Acquired for a research image collection, with no referral diagnosis · on a questionnaire the patient reported a personal history of skin cancer and a personal history of cancer · a male patient age 77 · the patient says their skin reddens with sun exposure.
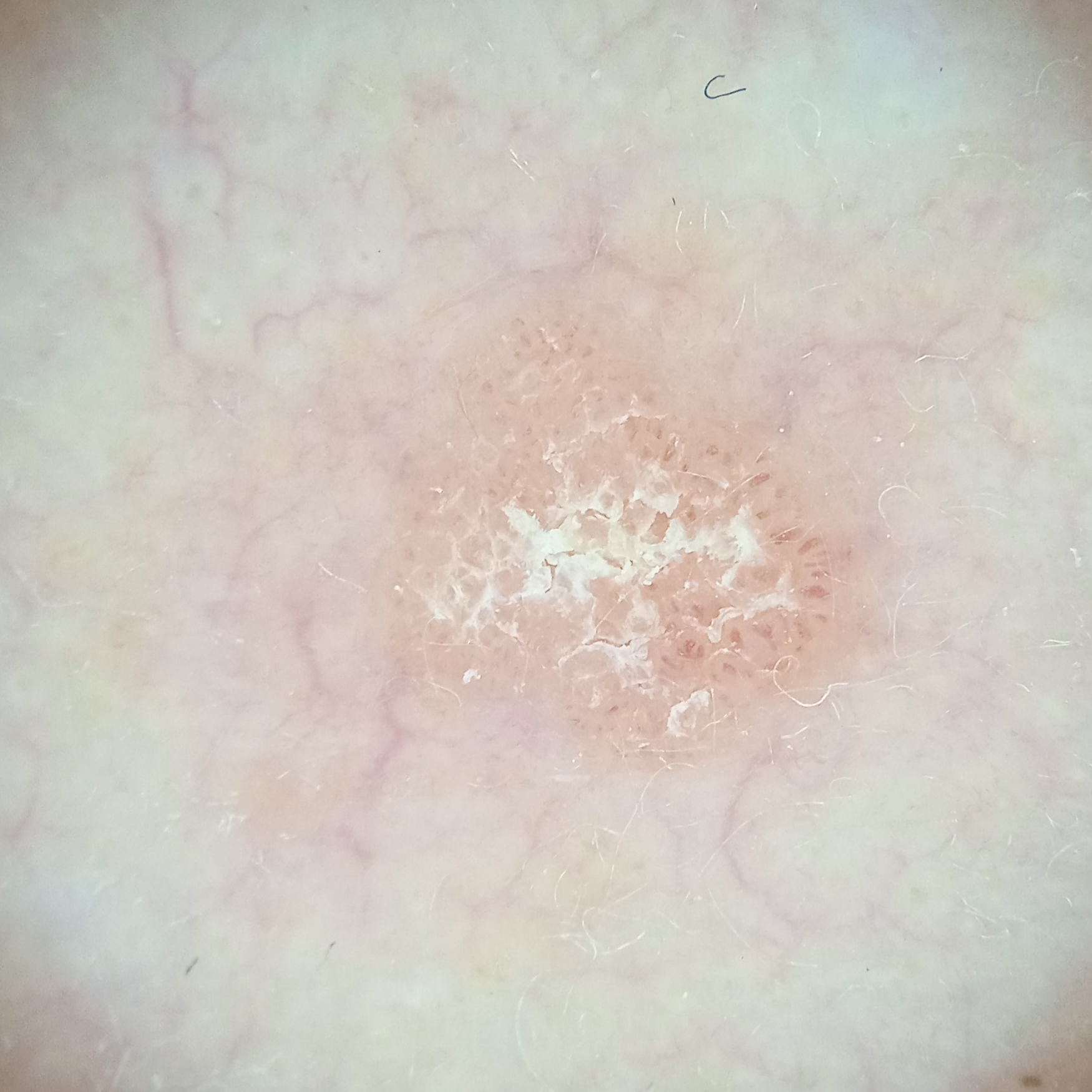Q: What is the anatomic site?
A: the face
Q: How large is the lesion?
A: 4.3 mm
Q: What was the diagnosis?
A: actinic keratosis (dermatologist consensus)